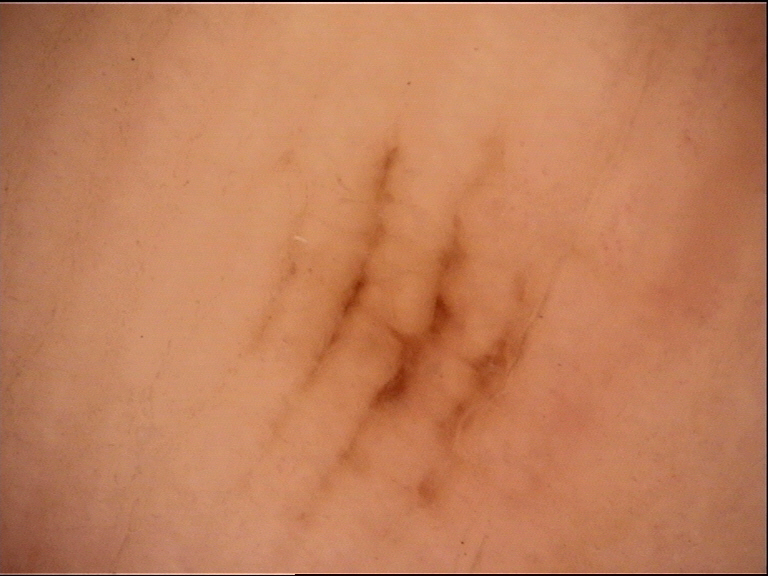Classified as an acral junctional nevus.